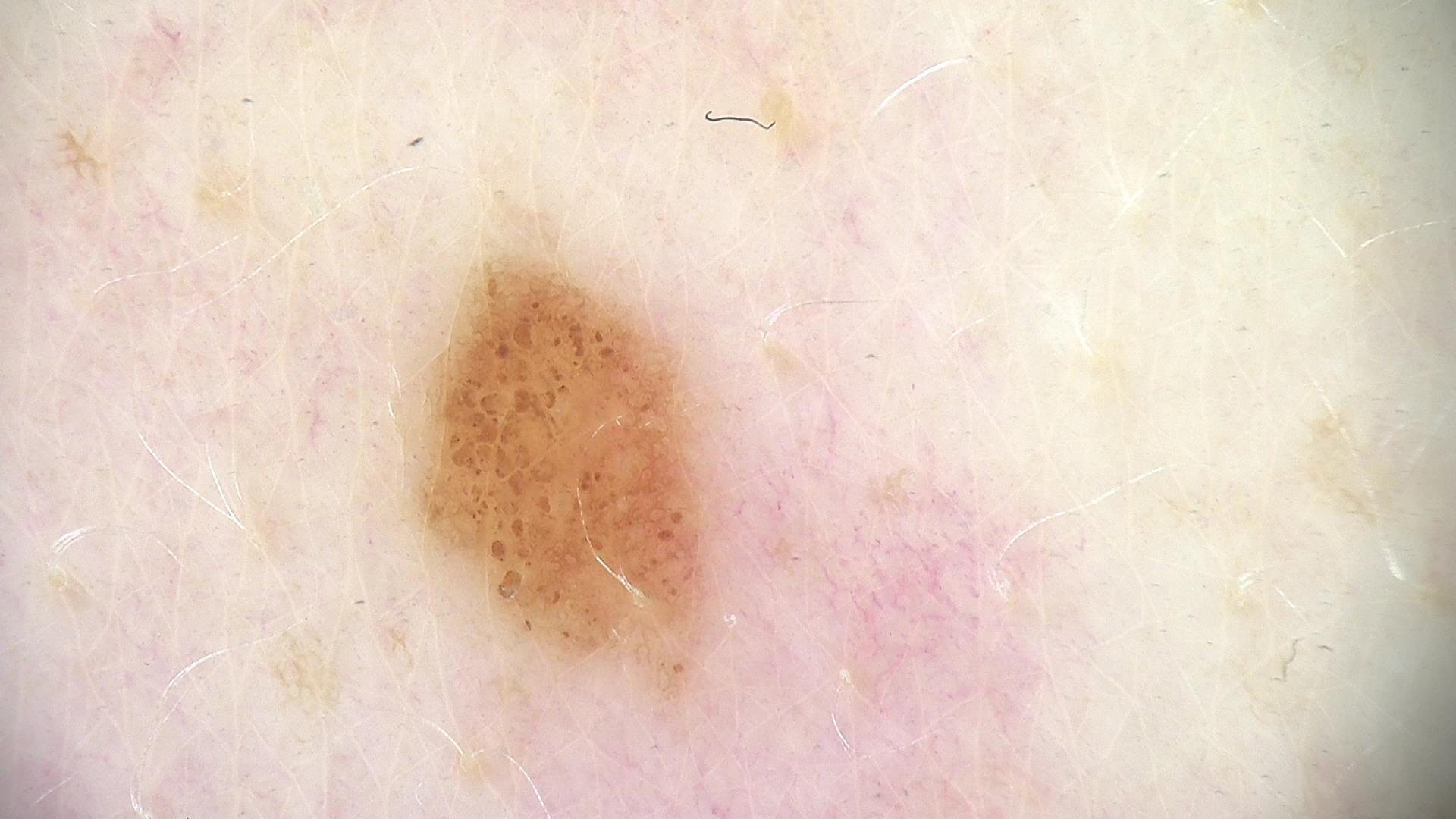{"lesion_type": {"main_class": "banal", "pattern": "compound"}, "diagnosis": {"name": "compound nevus", "code": "cb", "malignancy": "benign", "super_class": "melanocytic", "confirmation": "expert consensus"}}